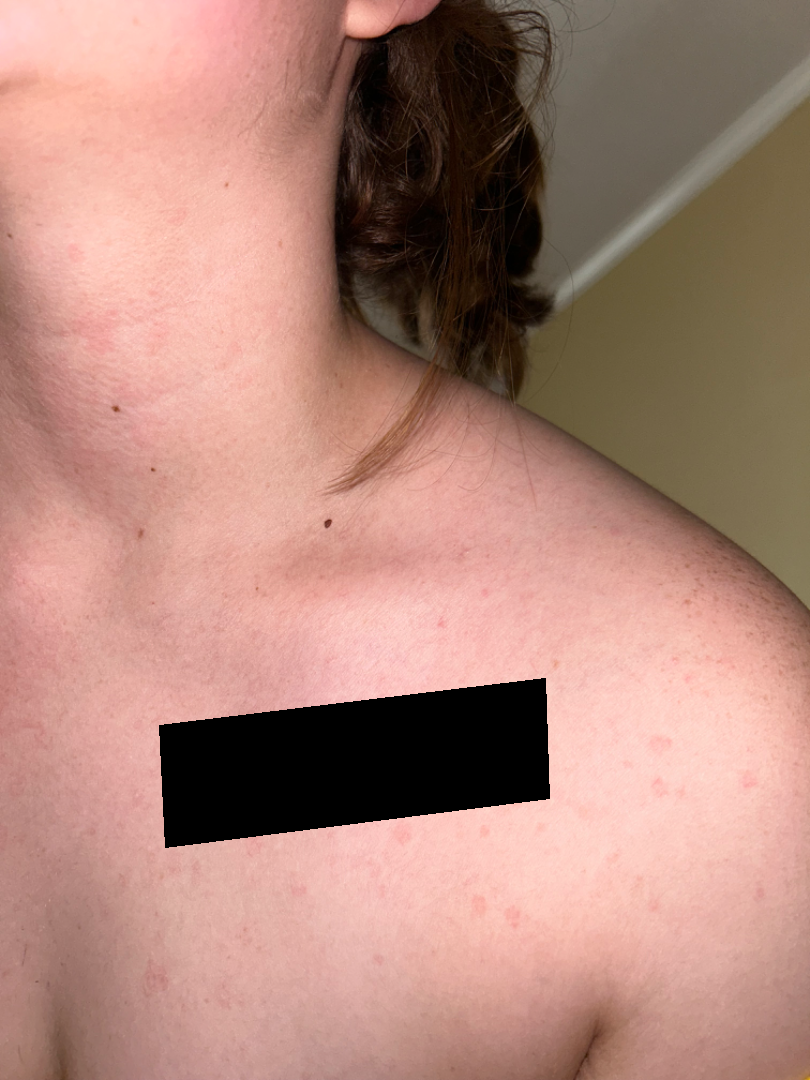Reviewed remotely by three dermatologists: the differential is split between Contact dermatitis and Tinea Versicolor; less probable is Pityriasis rosea; less likely is Drug Rash.